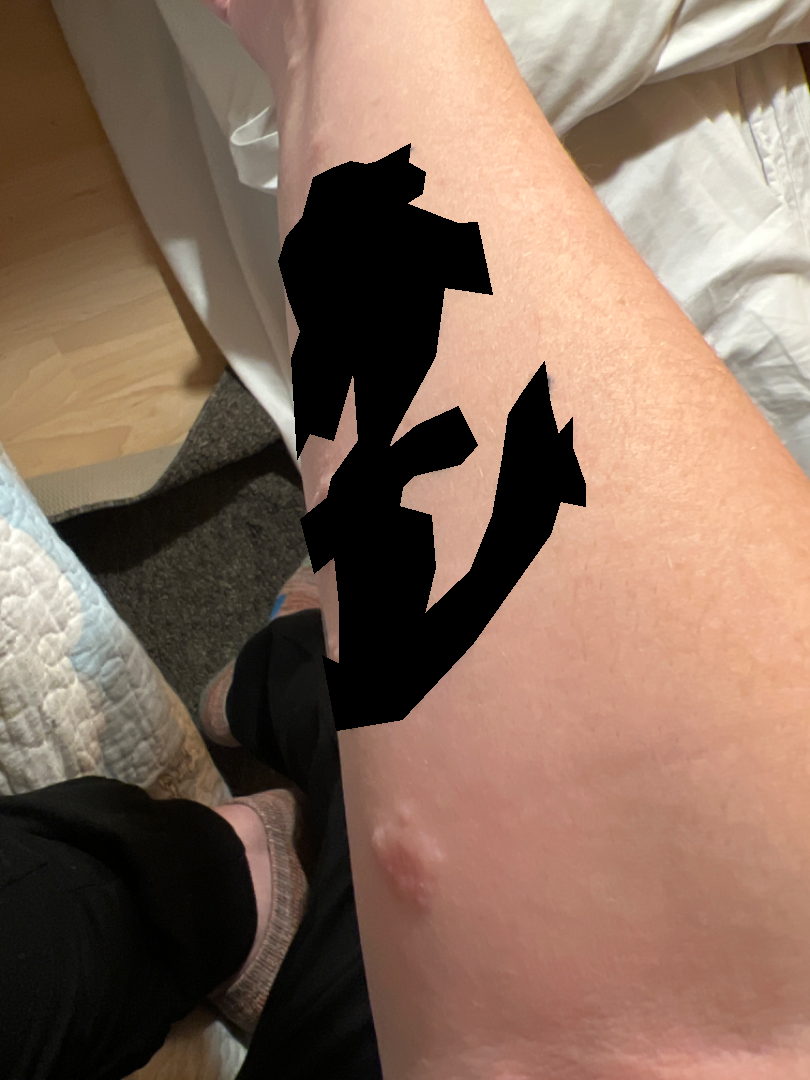Findings:
- location · arm
- contributor · female, age 30–39
- view · at an angle
- differential · Cutaneous sarcoidosis and Allergic Contact Dermatitis were each considered, in no particular order